A dermoscopic image of a skin lesion: 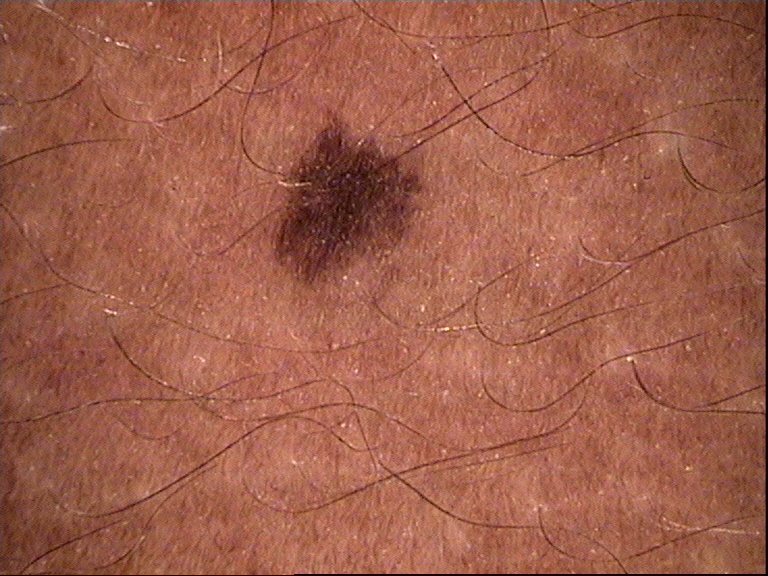Labeled as a benign lesion — a dysplastic junctional nevus.